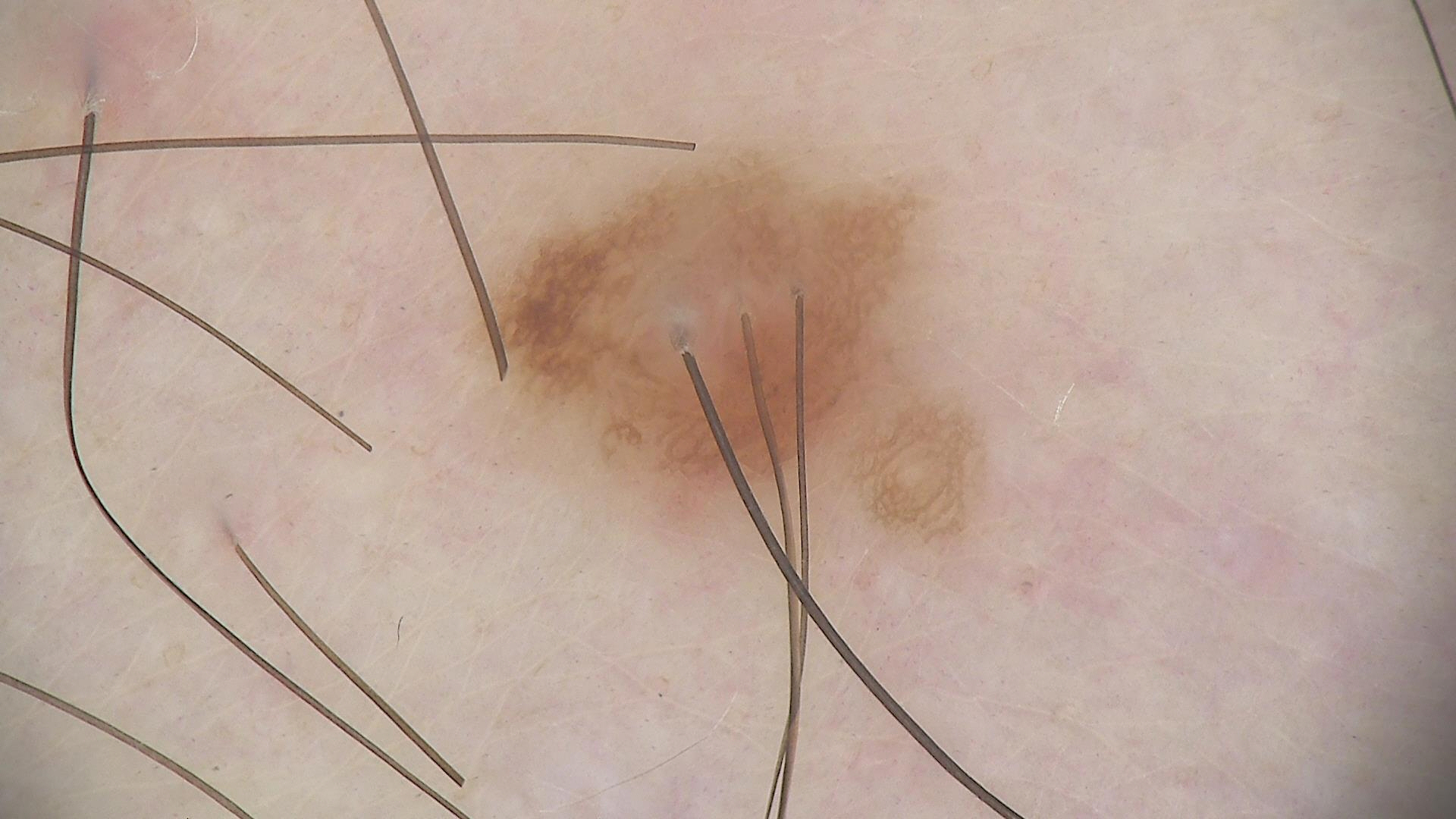image=dermatoscopy
assessment=compound nevus (expert consensus)